A female subject roughly 35 years of age. A dermoscopy image of a single skin lesion.
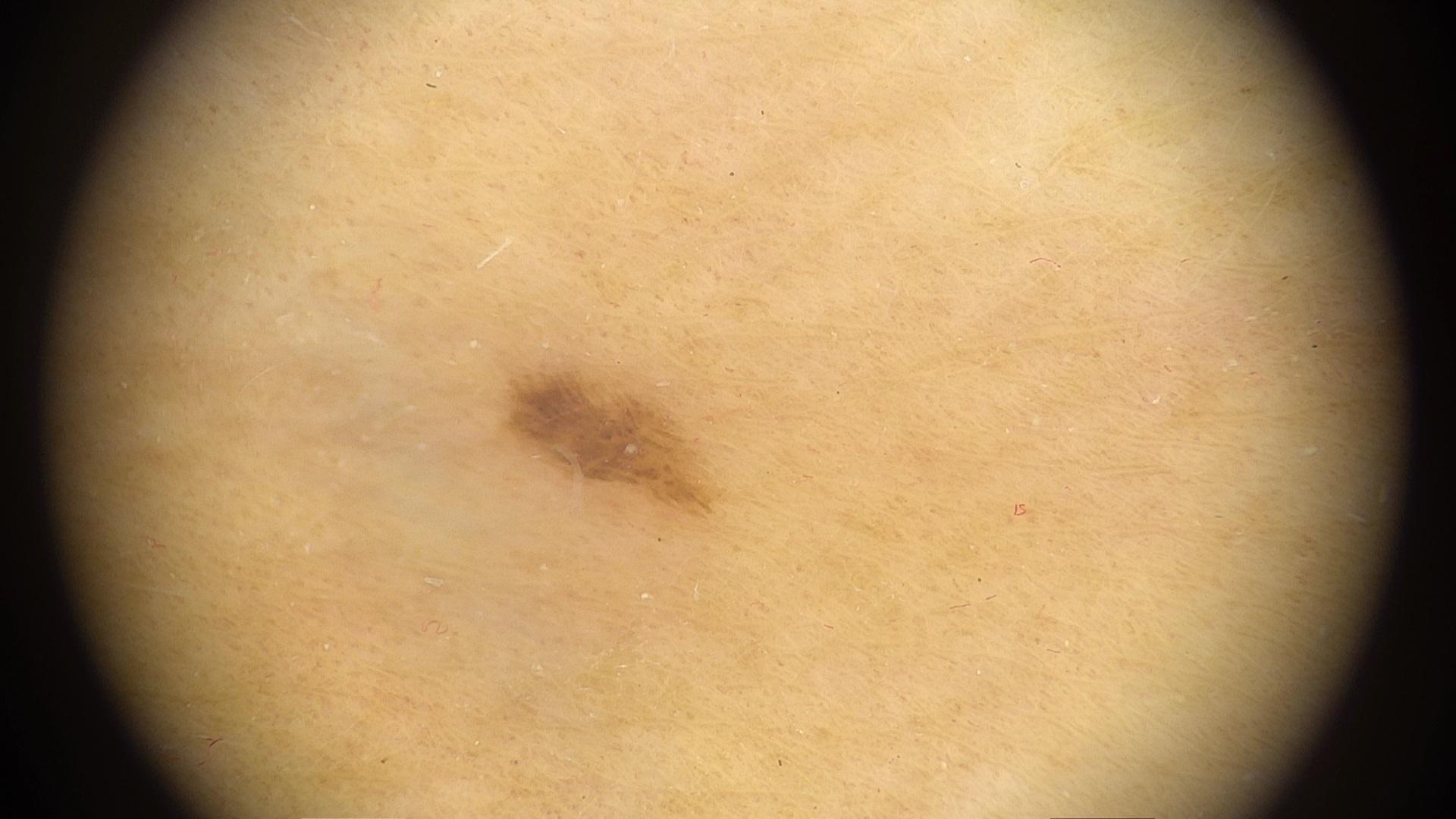{"diagnosis": {"name": "Nevus", "malignancy": "benign", "confirmation": "expert clinical impression", "lineage": "melanocytic"}}